Texture is reported as raised or bumpy · an image taken at a distance · the affected area is the front of the torso · self-categorized by the patient as a rash · the condition has been present for one to four weeks · the patient is 30–39, female · no relevant systemic symptoms · the contributor notes enlargement, itching and burning: 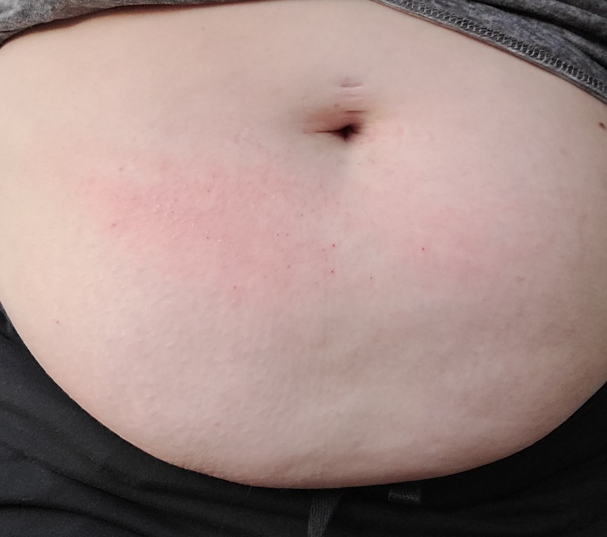The image was not sufficient for the reviewer to characterize the skin condition.